The affected area is the front of the torso. This is a close-up image: 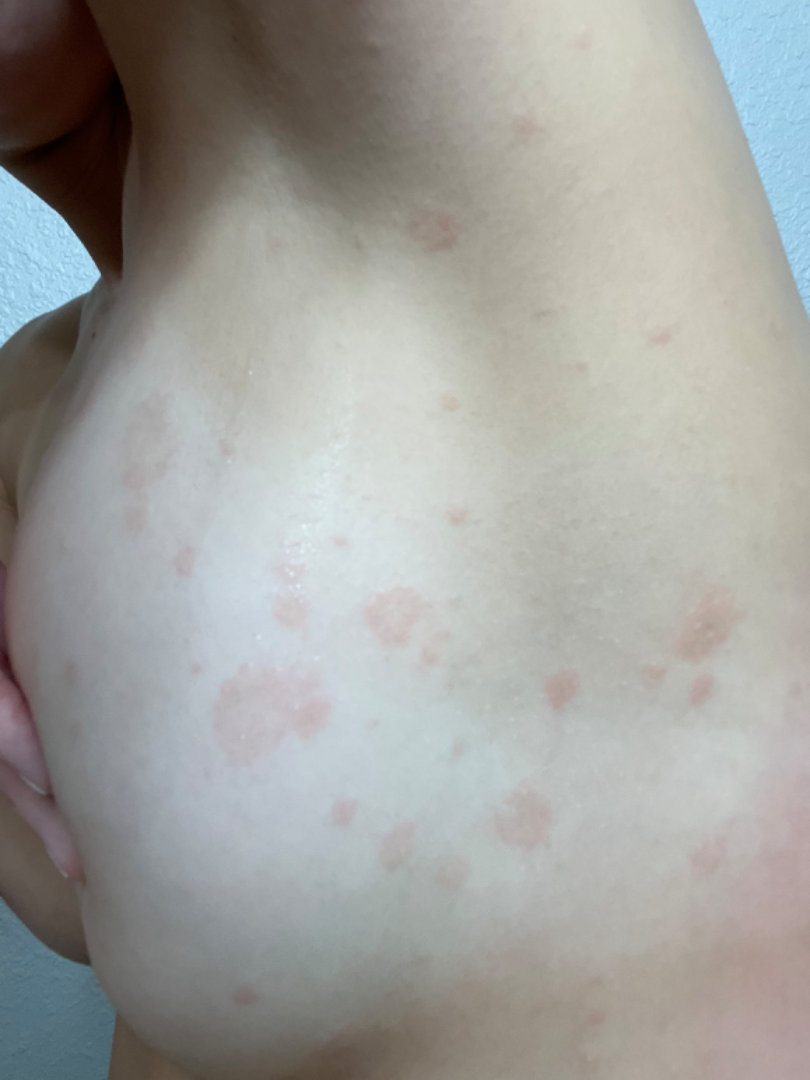Patient information: The lesion is described as flat. Self-categorized by the patient as a rash. The patient indicates enlargement. Review: The leading impression is Pityriasis rosea.